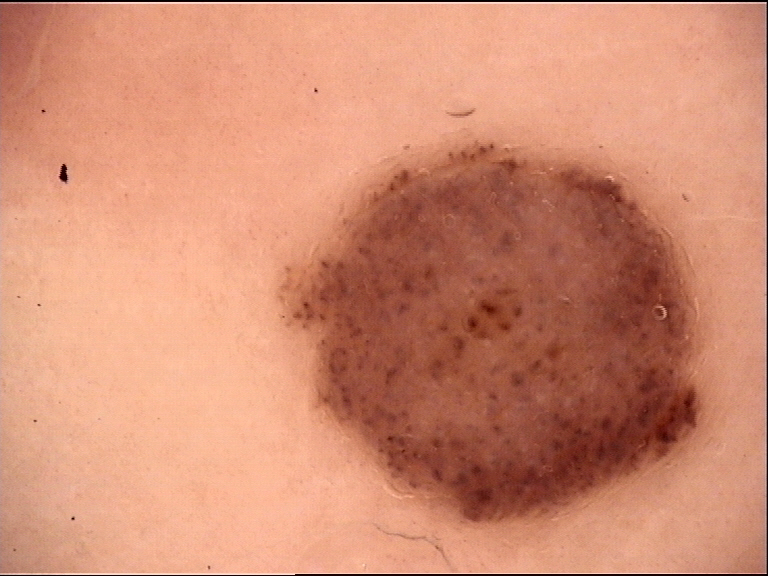* diagnostic label · compound nevus (expert consensus)